This is a close-up image. Located on the back of the hand, arm and leg:
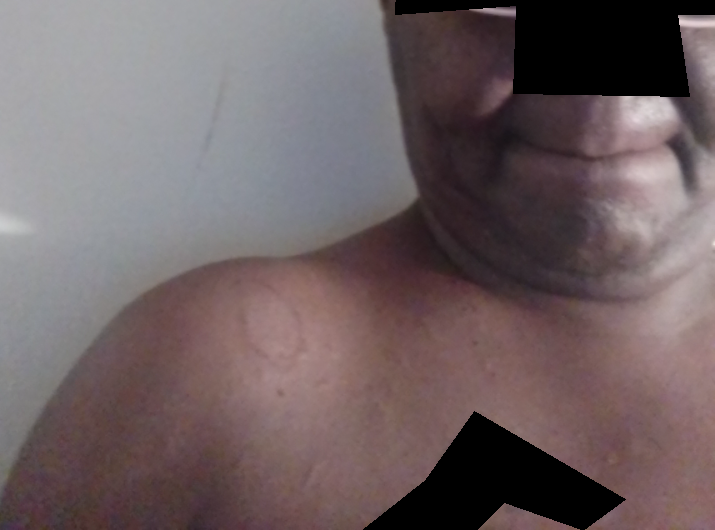Findings:
Diagnostic features were not clearly distinguishable in this photograph.
Background:
Skin tone: FST V. The patient considered this a rash.